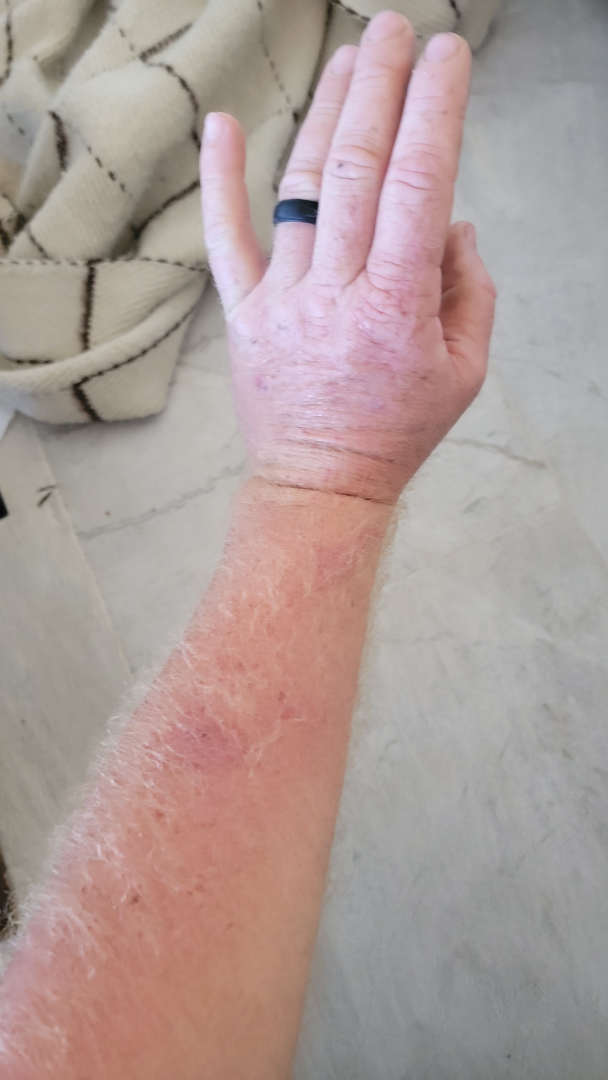assessment = indeterminate
subject = male, age 40–49
patient-reported symptoms = itching
anatomic site = arm and leg
framing = at a distance
patient describes the issue as = a rash
texture = raised or bumpy